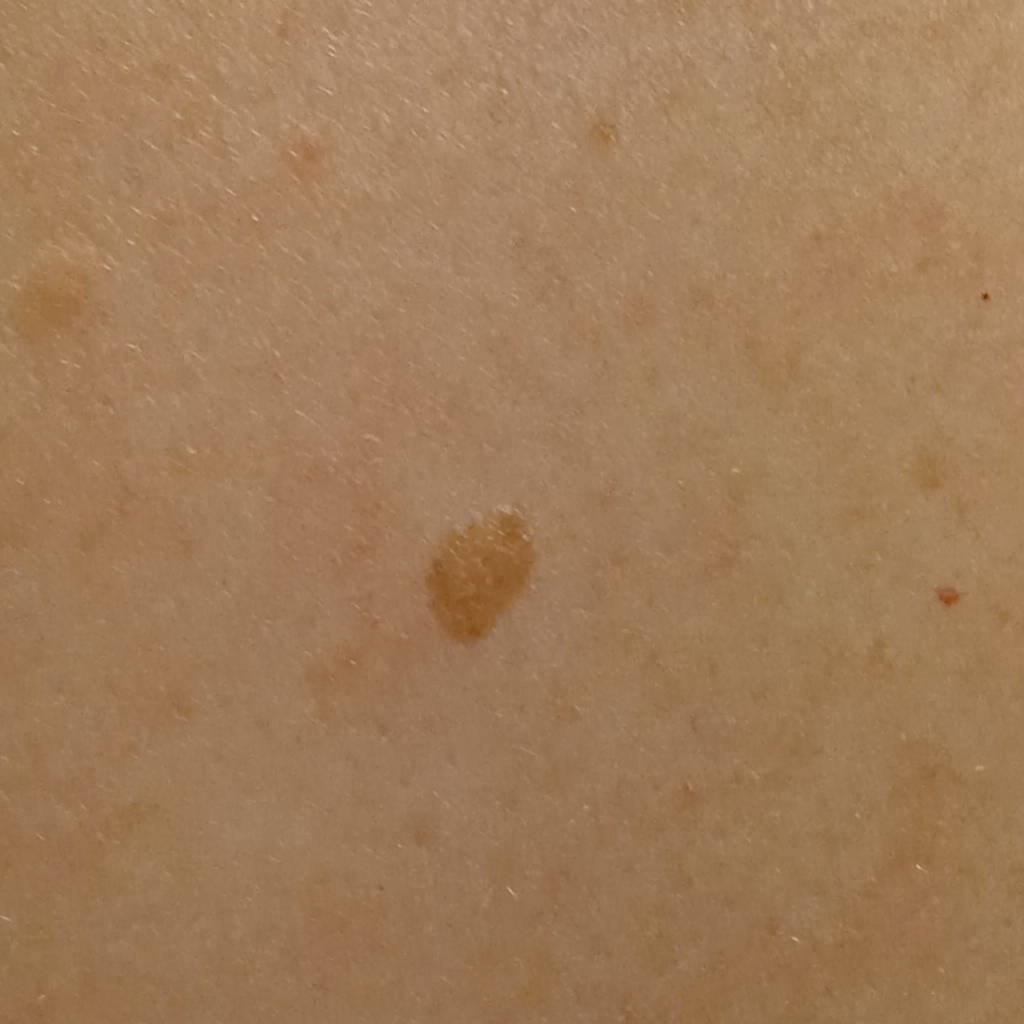Clinical context: By self-report, a family history of skin cancer, a personal history of cancer, a personal history of skin cancer, and no sunbed use. Collected as part of a research study, without a referral diagnosis. A female subject age 54. The lesion involves the back. Conclusion: The diagnostic impression was a seborrheic keratosis.